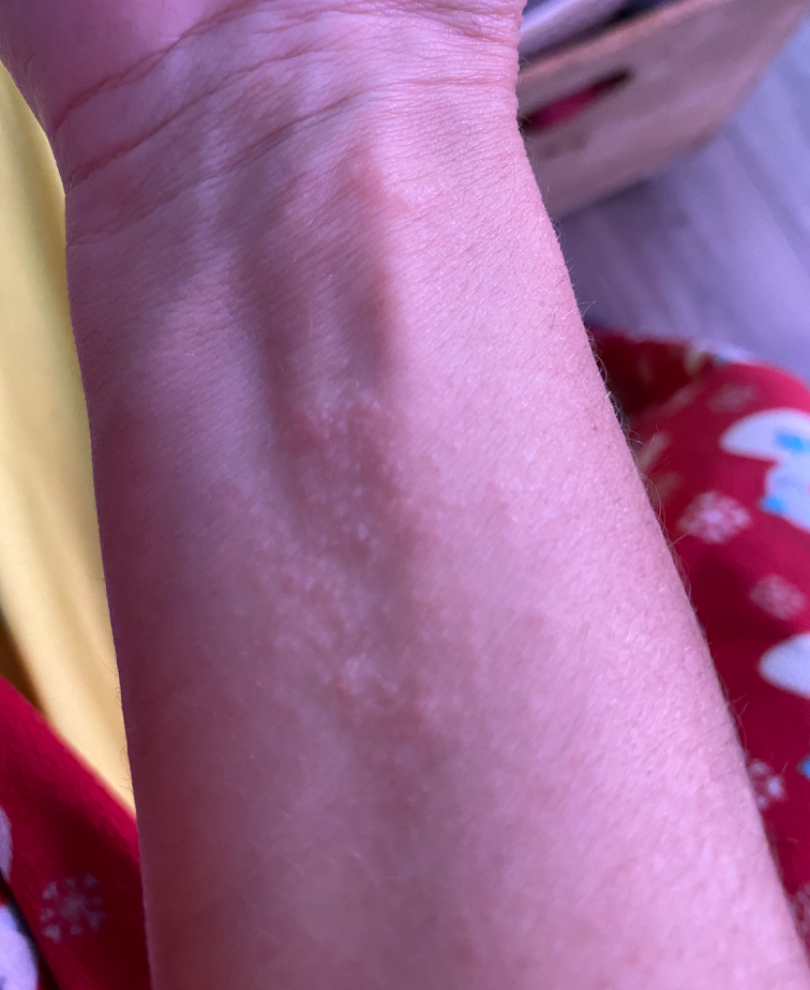{
  "patient_category": "a rash",
  "duration": "about one day",
  "body_site": [
    "back of the hand",
    "arm"
  ],
  "shot_type": "close-up",
  "systemic_symptoms": "none reported",
  "texture": [
    "flat",
    "raised or bumpy"
  ],
  "symptoms": "bothersome appearance",
  "patient": "female, age 40–49",
  "differential": {
    "leading": [
      "Eczema"
    ],
    "considered": [
      "Allergic Contact Dermatitis"
    ]
  }
}